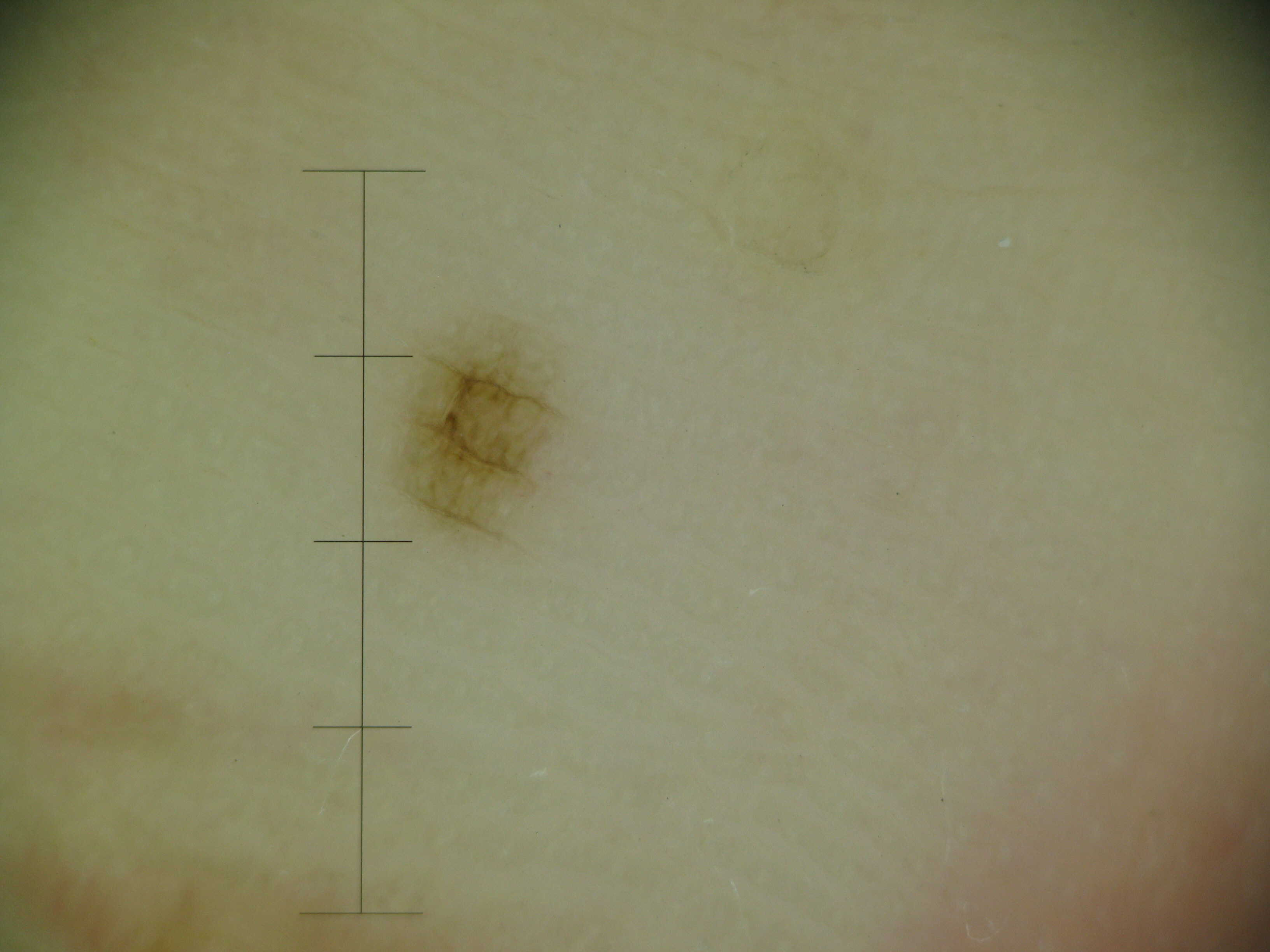The diagnostic label was an acral junctional nevus.